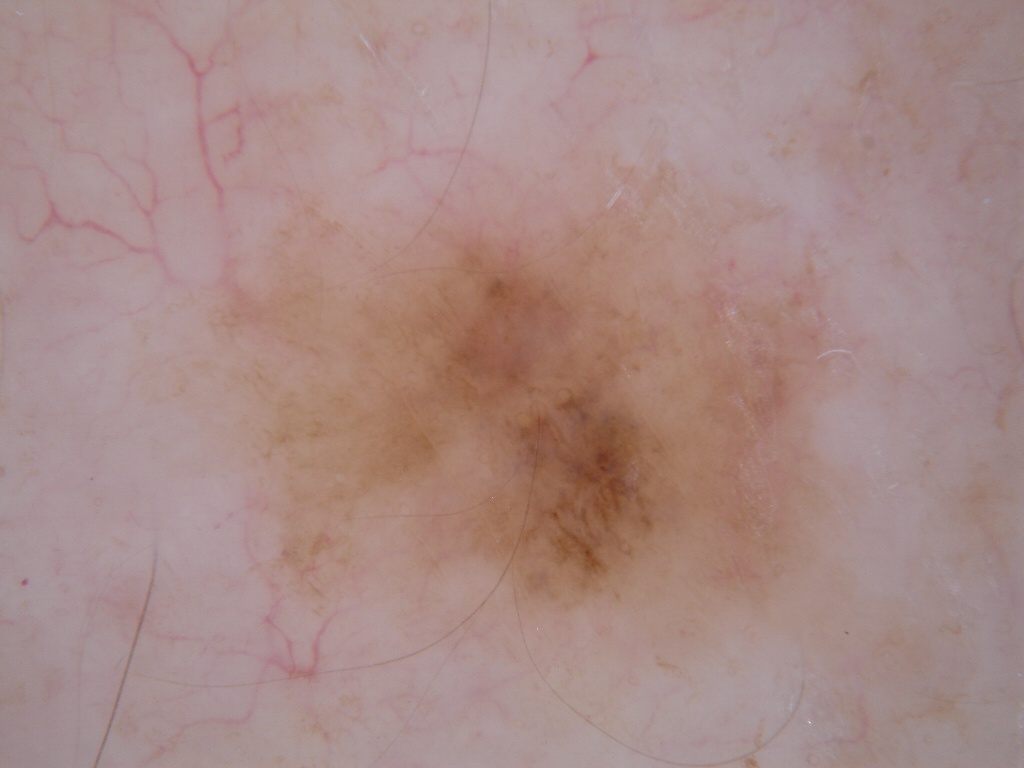Findings: A dermoscopy image of a single skin lesion. A female subject aged around 60. Dermoscopic assessment notes pigment network and streaks; no negative network, globules, or milia-like cysts. Lesion location: <bbox>132, 113, 911, 739</bbox>. Conclusion: The lesion was assessed as a melanocytic nevus.